A dermoscopic photograph of a skin lesion:
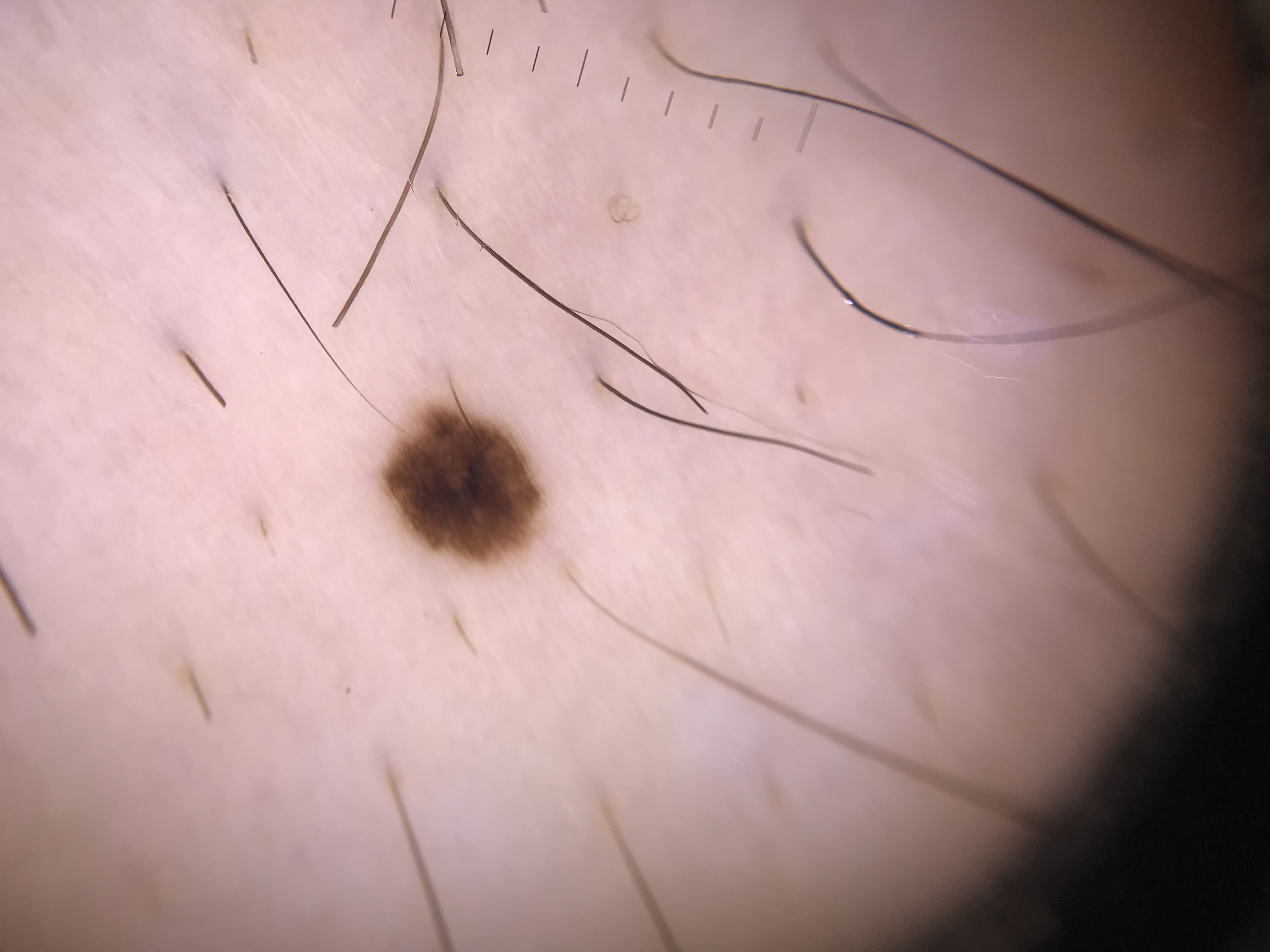The diagnosis was a benign lesion — a dysplastic junctional nevus.